A dermoscopic photograph of a skin lesion.
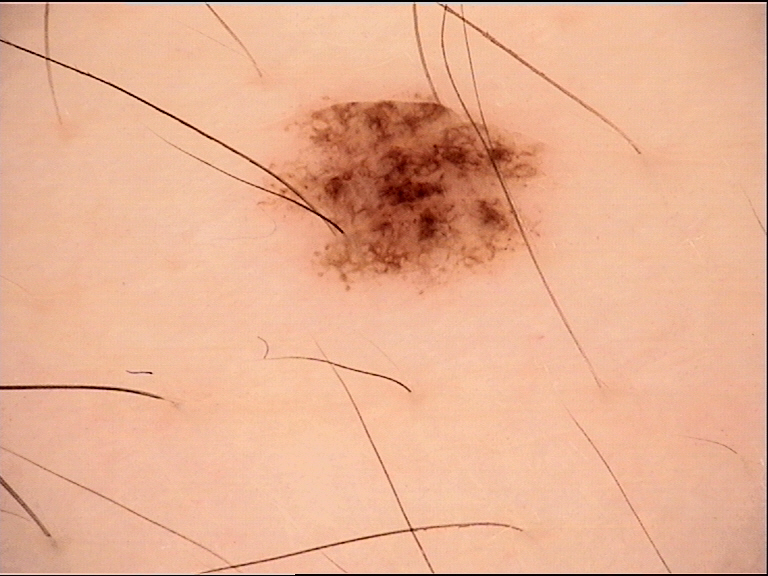Labeled as a benign lesion — a dysplastic junctional nevus.